Collected as part of a research study, without a referral diagnosis · a female patient aged 55 · a clinical close-up of a skin lesion:
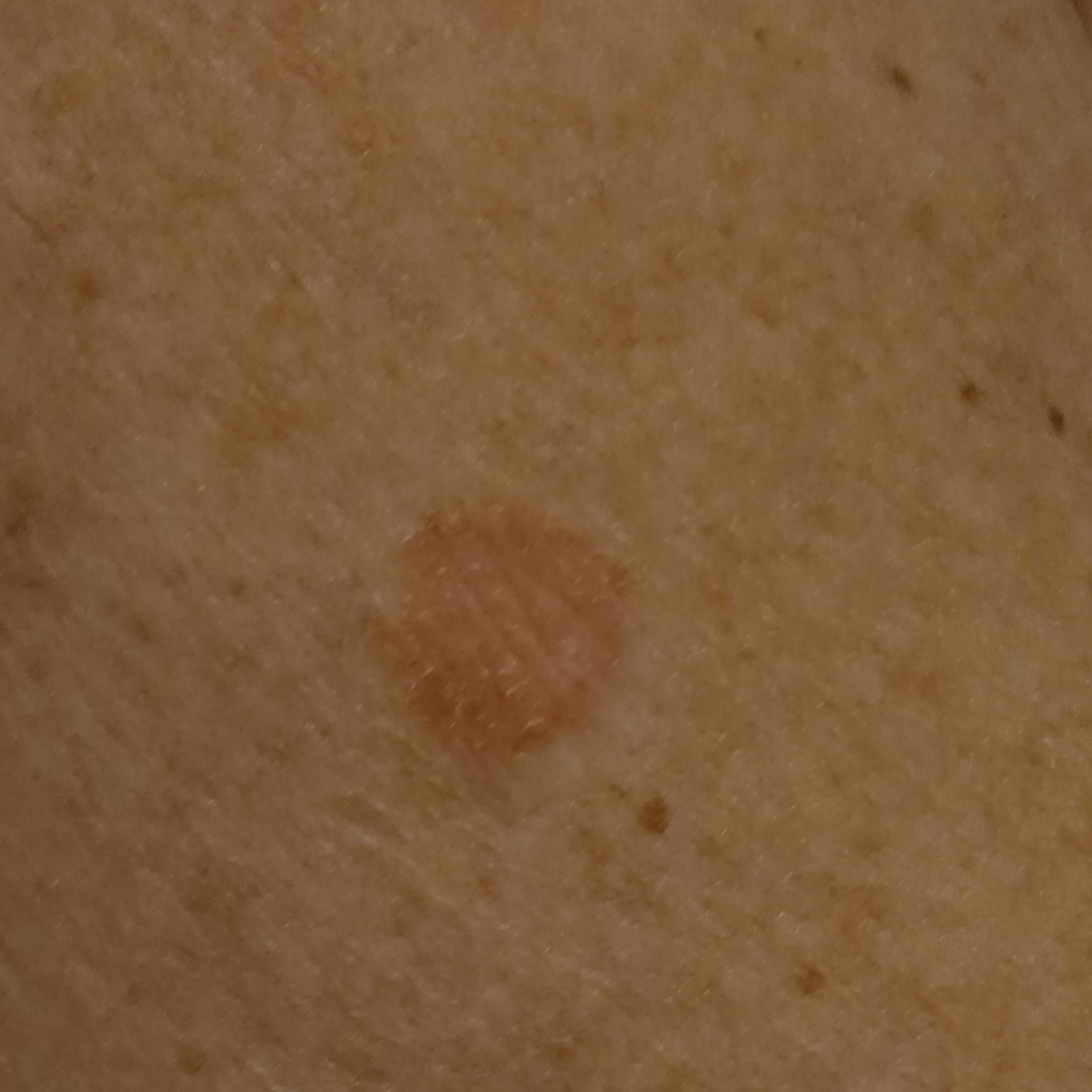anatomic site — an arm
diameter — 13.2 mm
assessment — basal cell carcinoma (dermatologist consensus)